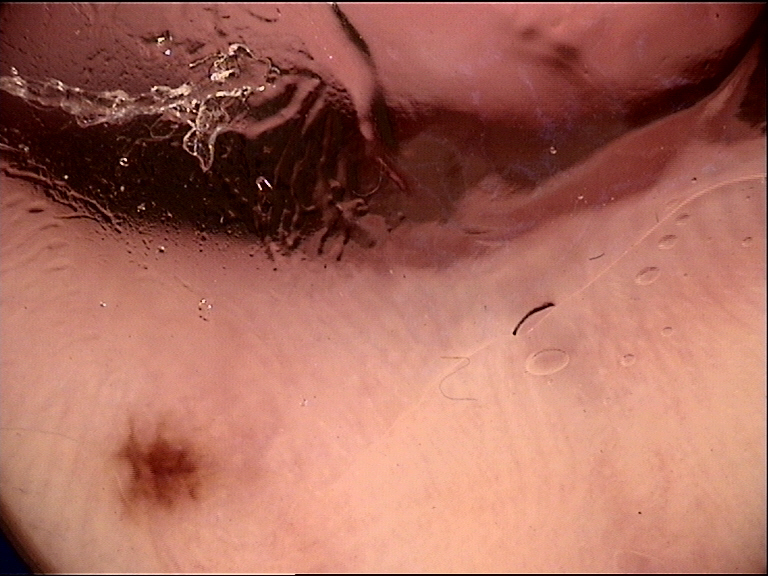- image: dermatoscopy
- class: acral dysplastic junctional nevus (expert consensus)